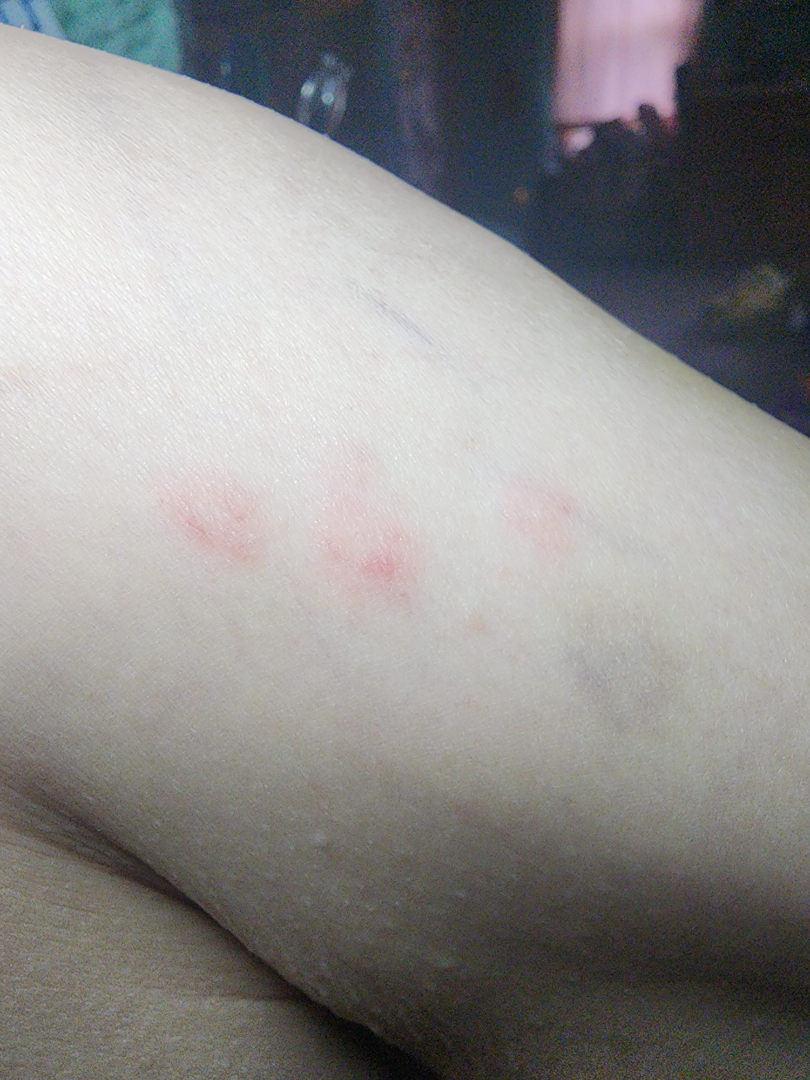Review: The skin findings could not be characterized from the image. Patient information: Close-up view. The condition has been present for less than one week. The contributor reports the lesion is raised or bumpy. The leg is involved.